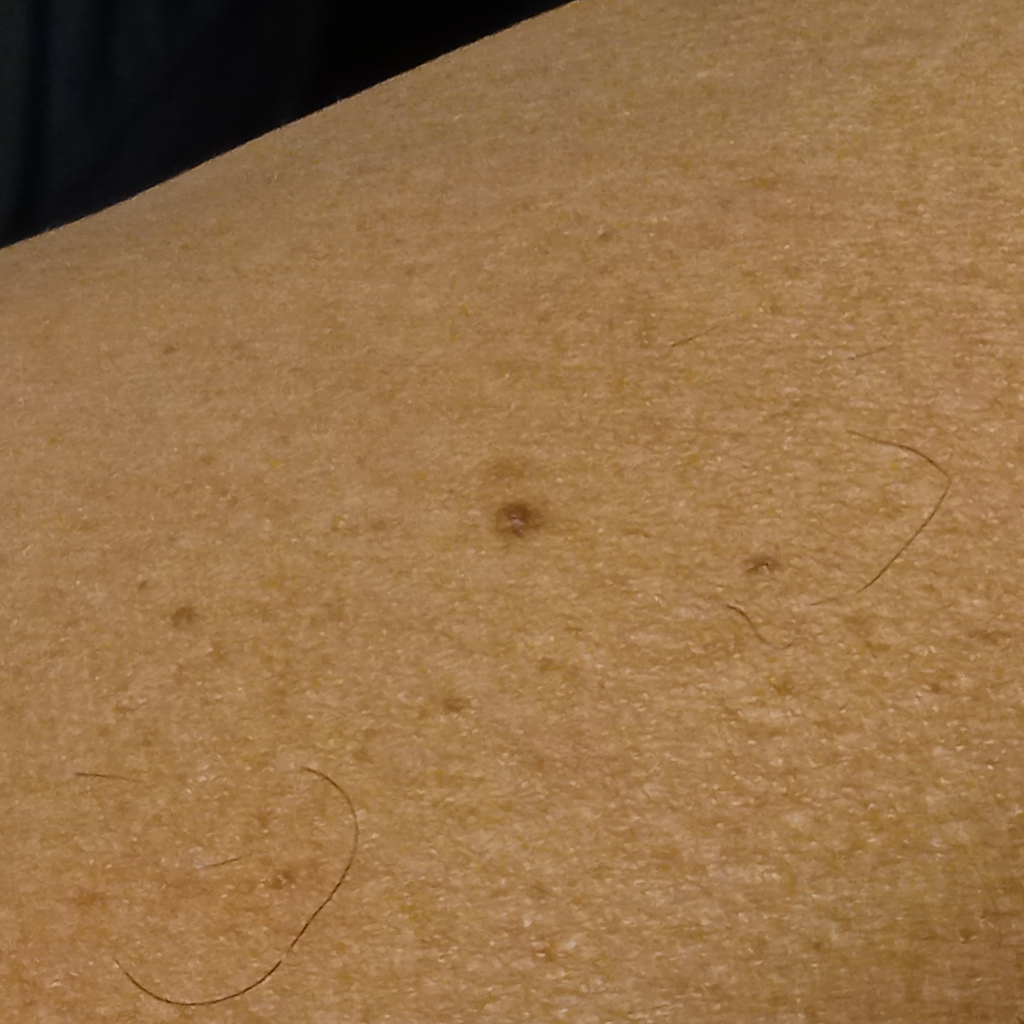subject = male, 54 years of age; relevant history = a personal history of cancer; modality = clinical photo; nevus count = a moderate number of melanocytic nevi; lesion size = 2.9 mm; assessment = melanocytic nevus (dermatologist consensus).